The lesion involves the back of the hand. Male patient, age 60–69. The photograph is a close-up of the affected area — 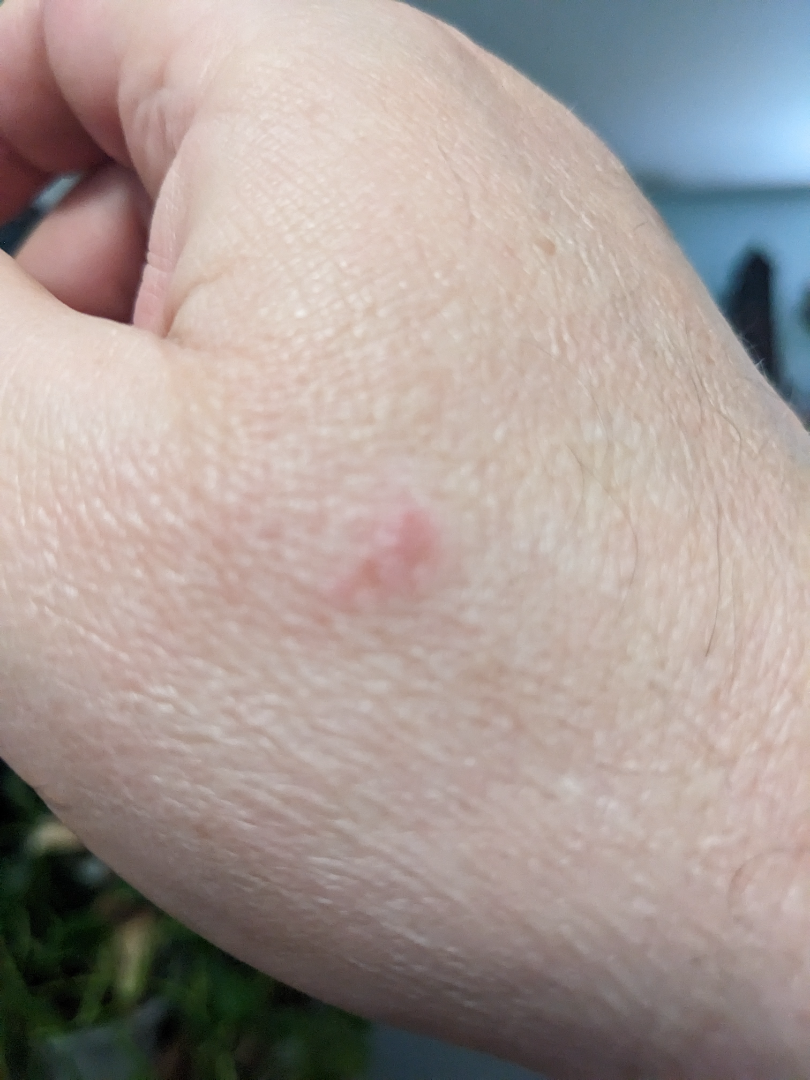Associated systemic symptoms include joint pain and fatigue. Fitzpatrick skin type II; non-clinician graders estimated MST 1 or 2. The patient reports the lesion is raised or bumpy and rough or flaky. The differential, in no particular order, includes Eczema, Insect Bite and Herpes Simplex.